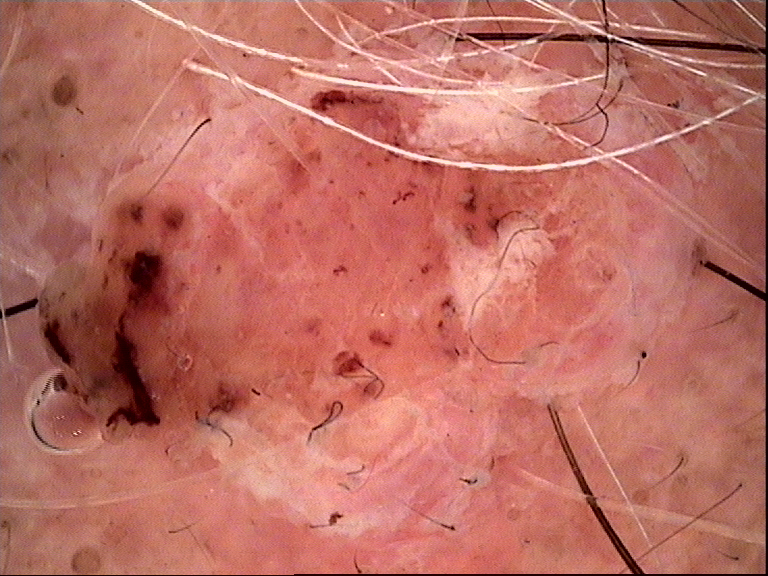{
  "lesion_type": {
    "main_class": "banal",
    "pattern": "dermal"
  },
  "diagnosis": {
    "name": "dermal nevus",
    "code": "db",
    "malignancy": "benign",
    "super_class": "melanocytic",
    "confirmation": "expert consensus"
  }
}